The lesion is described as raised or bumpy · this image was taken at a distance · the contributor notes the condition has been present for one to four weeks · the arm is involved:
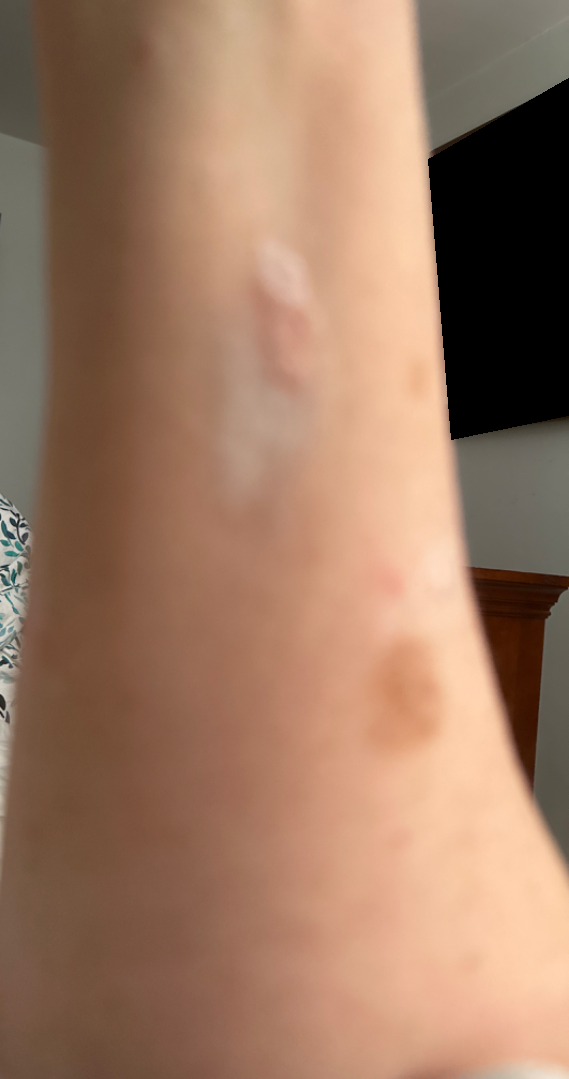<dermatology_case>
  <assessment>ungradable on photographic review</assessment>
</dermatology_case>